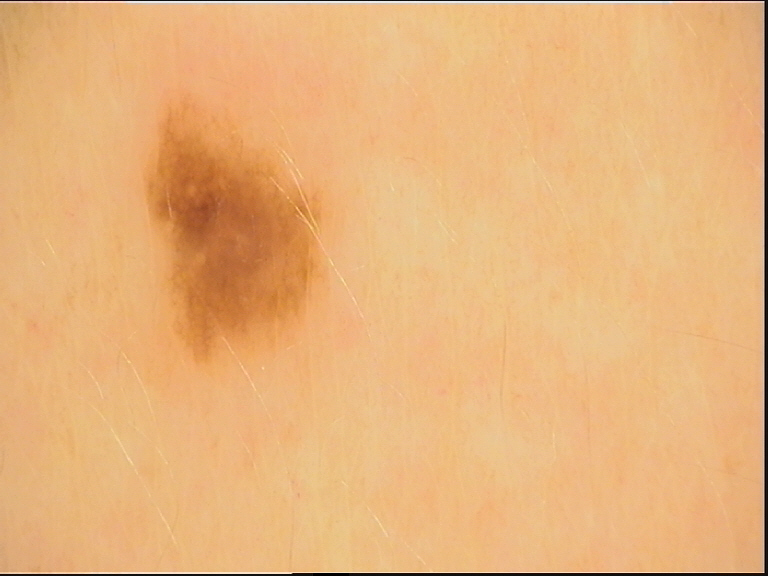Summary:
A dermatoscopic image of a skin lesion.
Impression:
Diagnosed as a dysplastic junctional nevus.